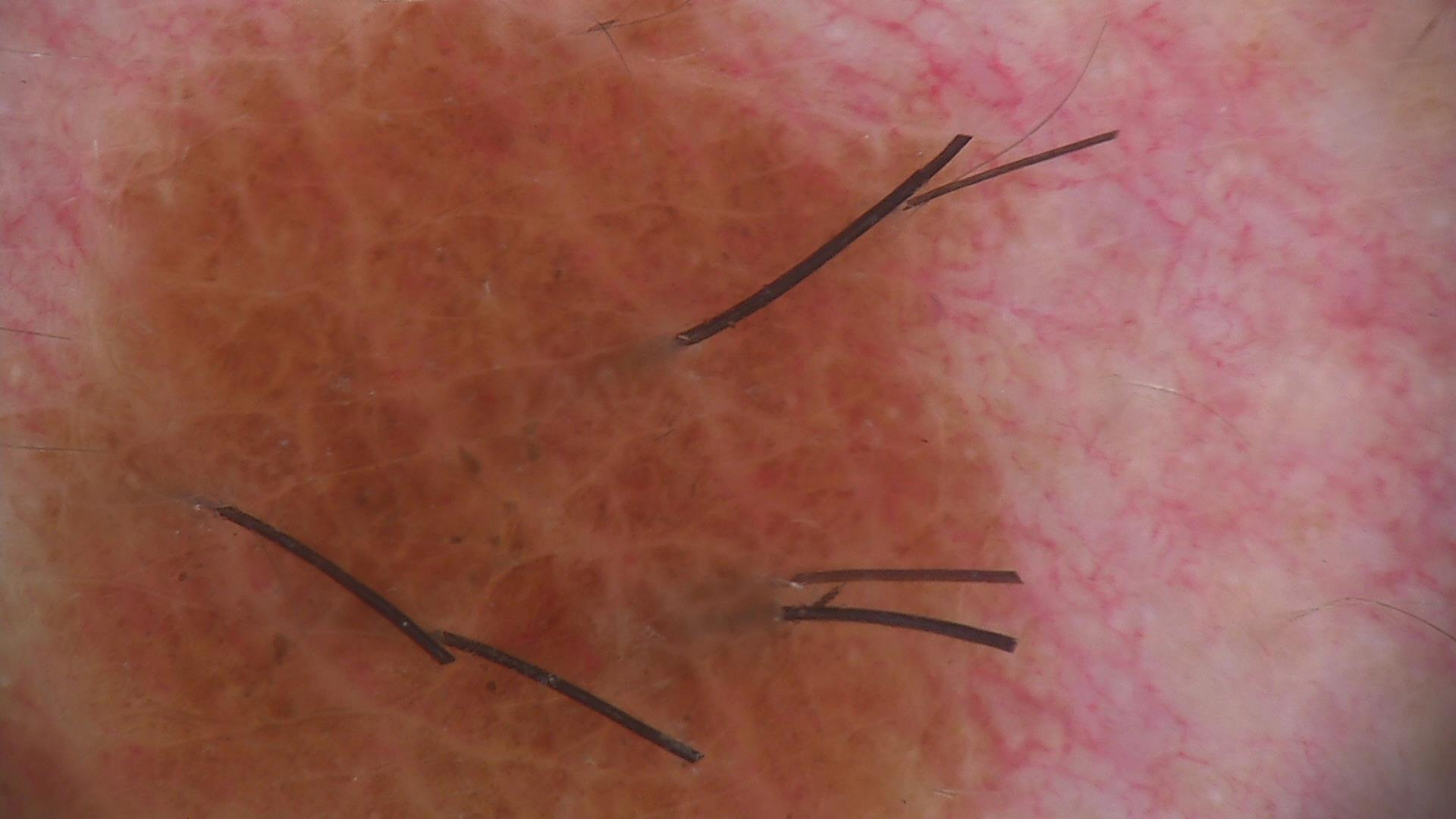imaging — dermoscopy | lesion type — banal | class — compound nevus (expert consensus).